A dermoscopic image of a skin lesion; the patient is a male aged approximately 50:
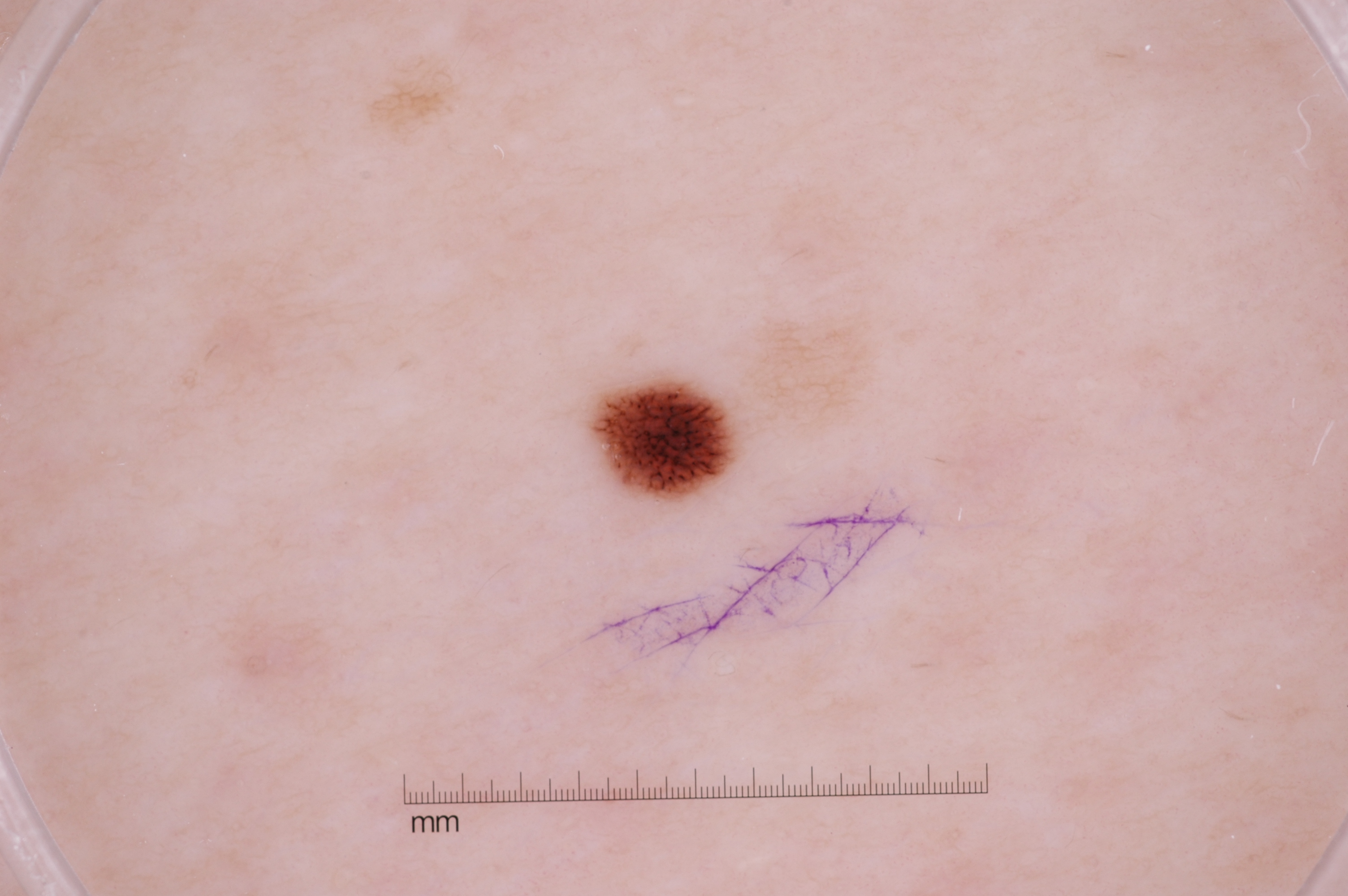| field | value |
|---|---|
| features | pigment network; absent: milia-like cysts, negative network, and streaks |
| lesion location | 590, 378, 726, 497 |
| assessment | a melanocytic nevus, a benign skin lesion |